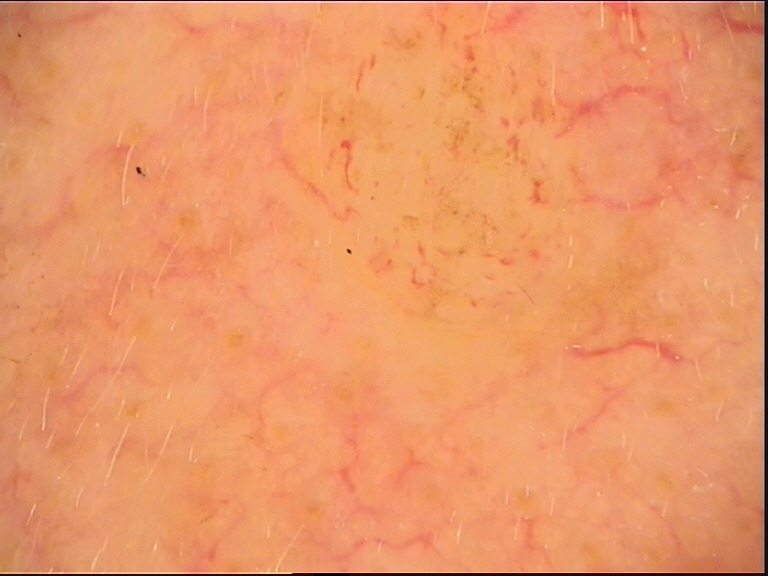Case:
* classification — banal
* label — dermal nevus (expert consensus)